A clinical close-up photograph of a skin lesion.
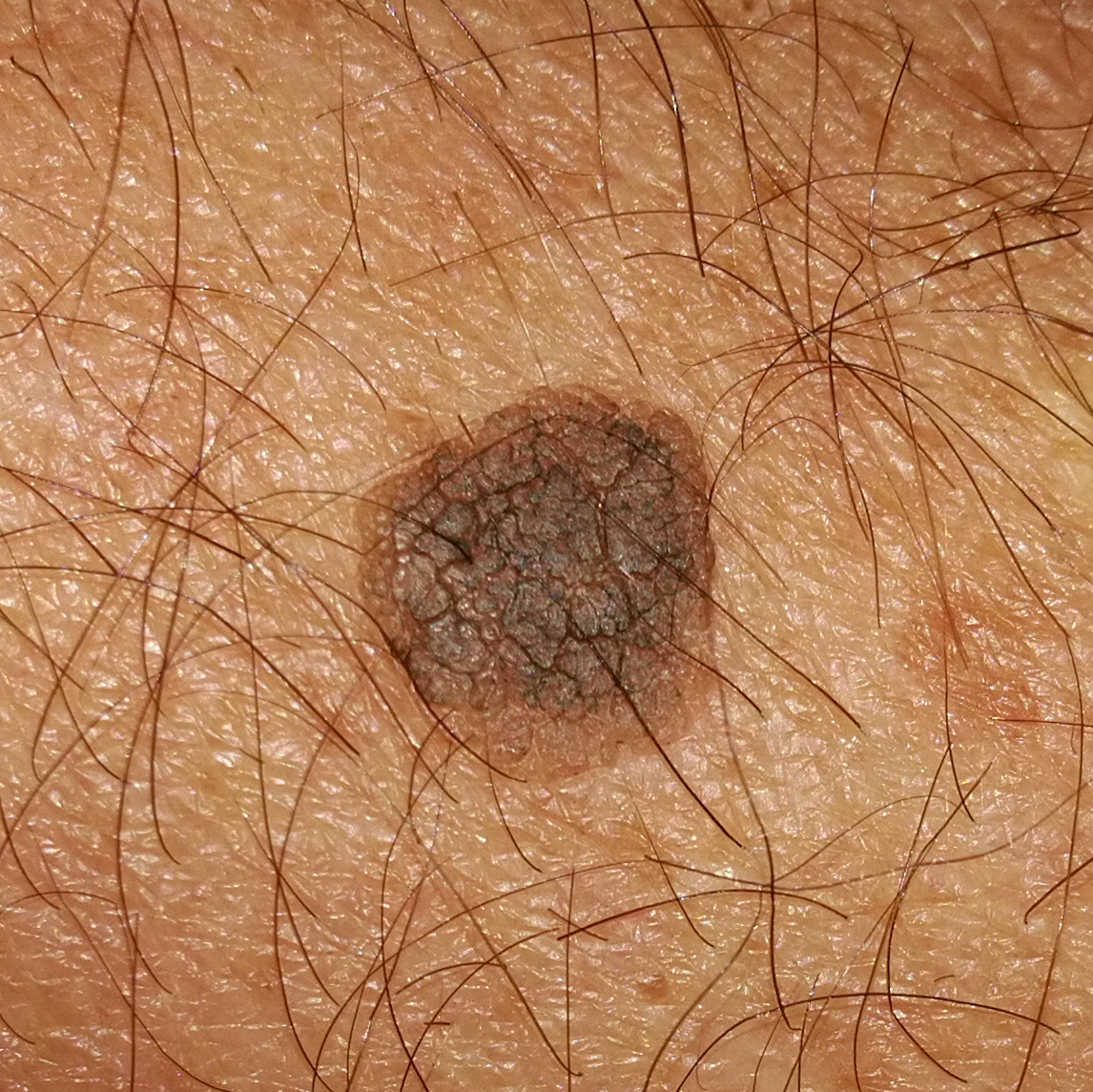{"diagnosis": {"name": "nevus", "code": "NEV", "malignancy": "benign", "confirmation": "clinical consensus"}}